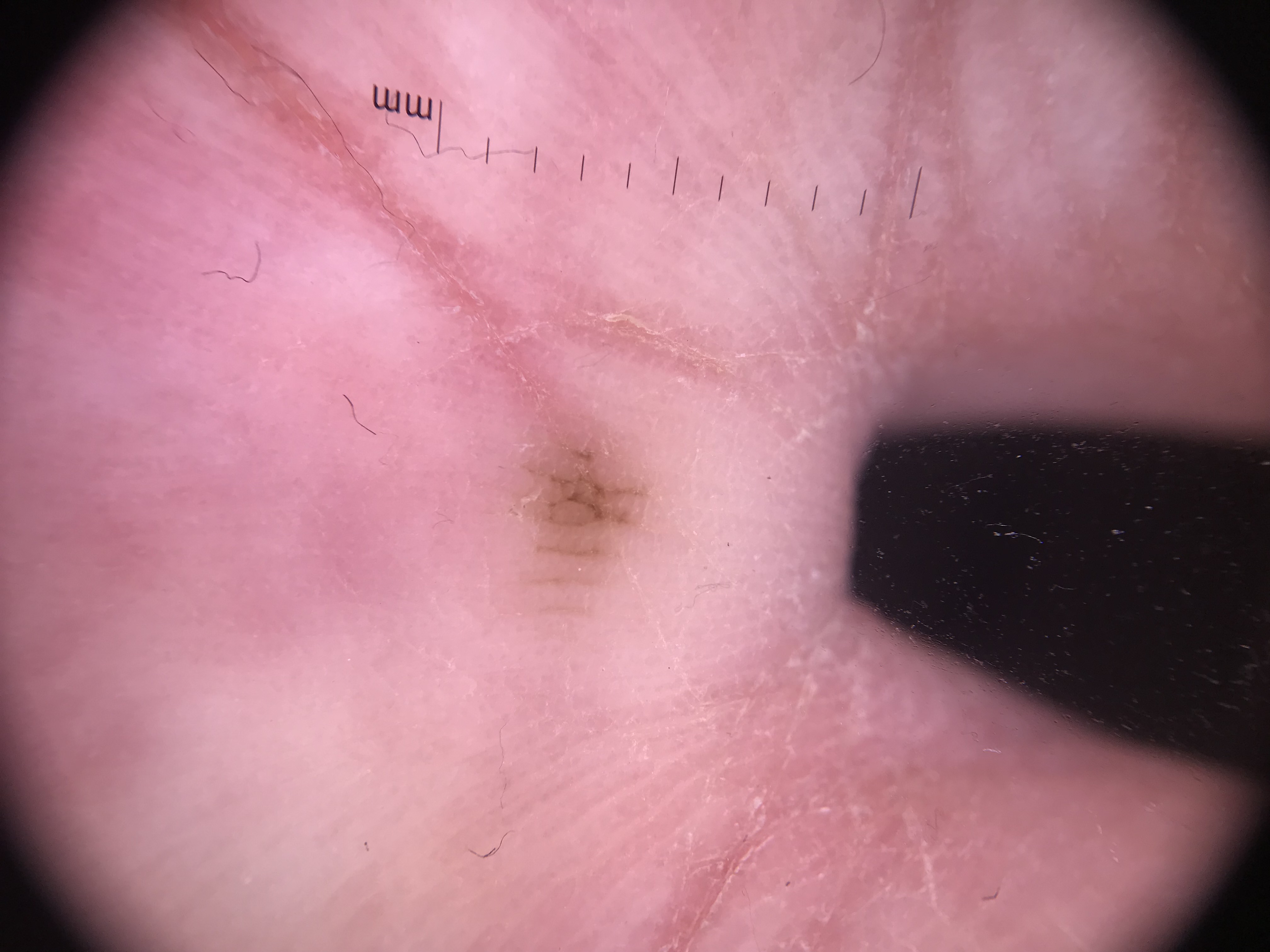Summary: A dermoscopic image of a skin lesion. The morphology is that of a banal lesion. Impression: Labeled as an acral junctional nevus.